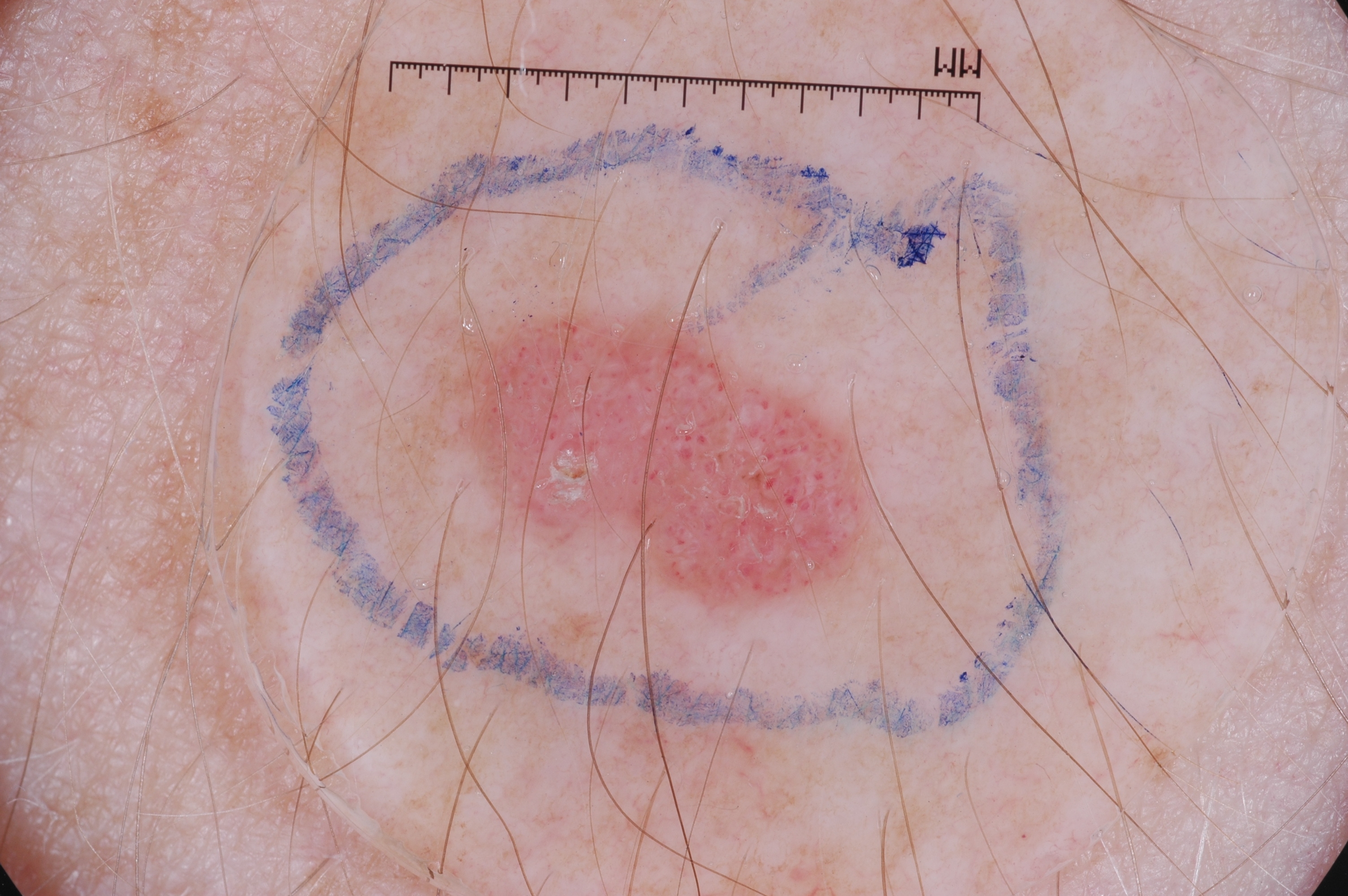The patient is a female about 45 years old. A skin lesion imaged with a dermatoscope. The lesion is located at x1=411, y1=301, x2=874, y2=602. Dermoscopic assessment notes milia-like cysts, with no streaks, pigment network, or negative network. Clinically diagnosed as a seborrheic keratosis, a benign skin lesion.